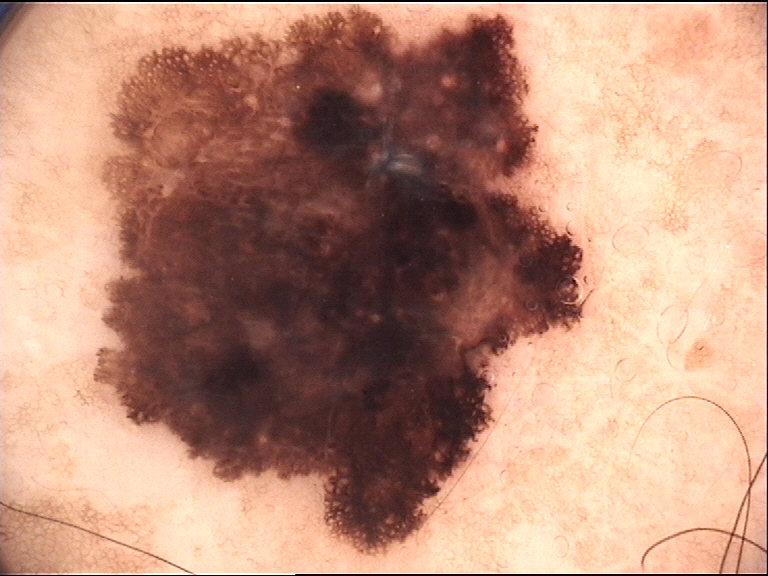| feature | finding |
|---|---|
| image type | dermatoscopy |
| label | melanoma (biopsy-proven) |